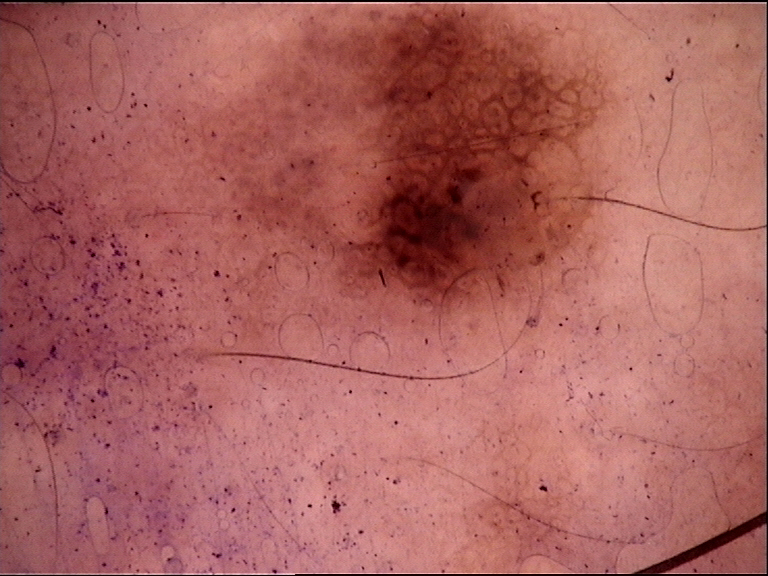| key | value |
|---|---|
| imaging | dermoscopy |
| diagnostic label | dysplastic junctional nevus (expert consensus) |